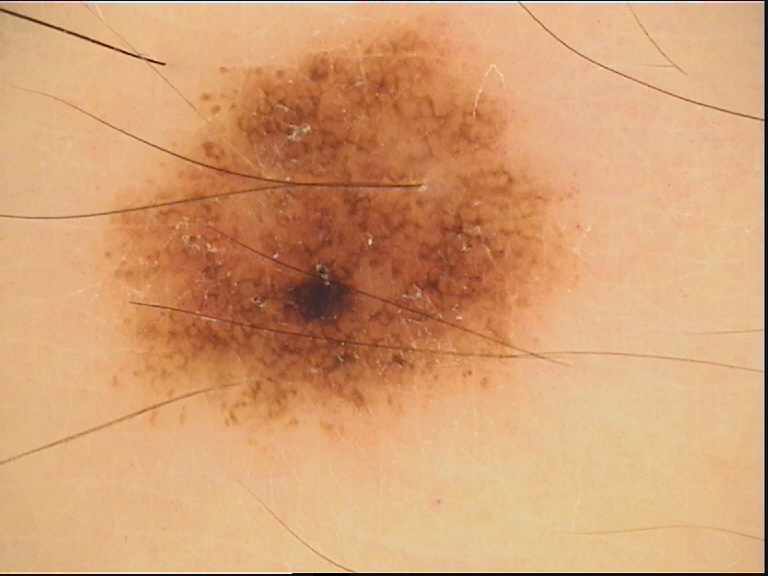class = dysplastic junctional nevus (expert consensus).